Located on the top or side of the foot. The patient is 40–49, female. The photograph was taken at an angle — 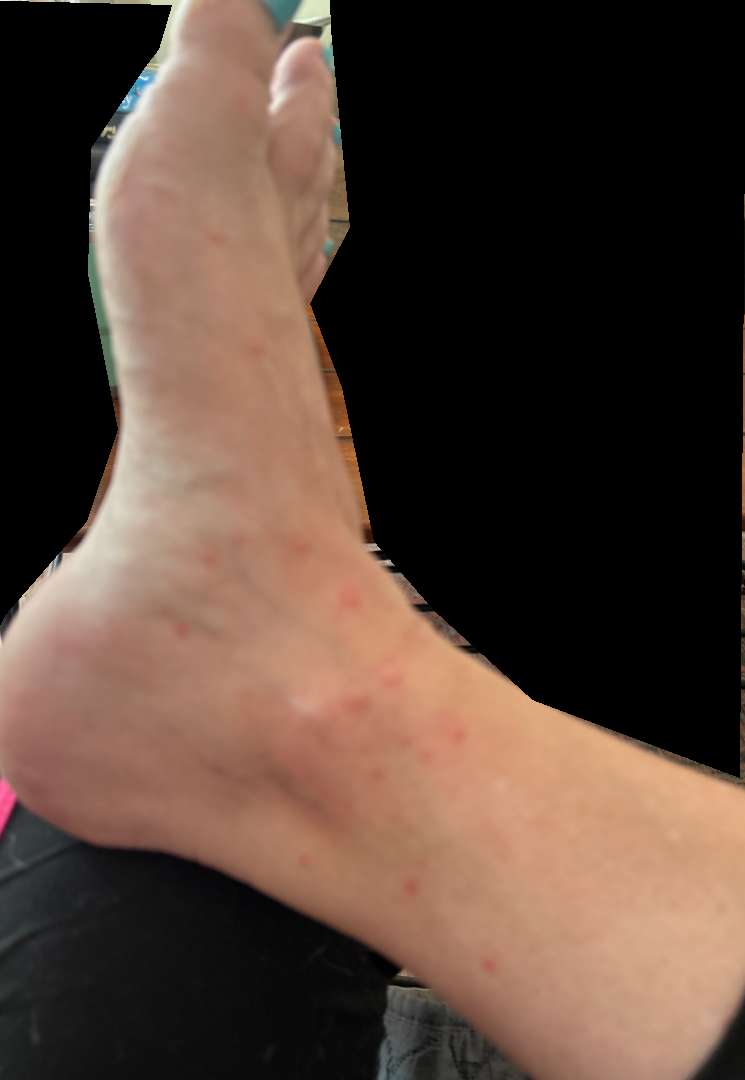Case summary:
* assessment — could not be assessed